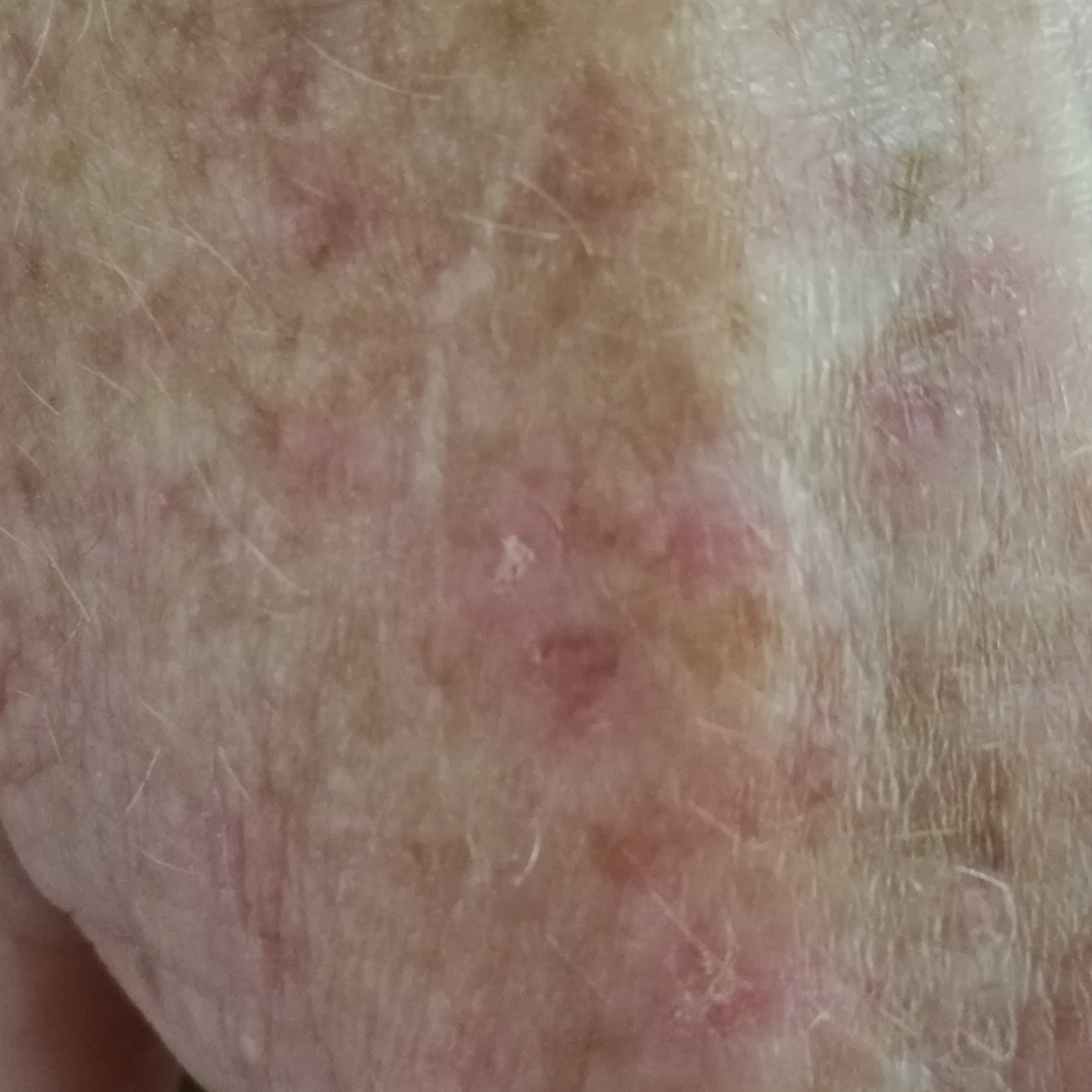{
  "image": "smartphone clinical photo",
  "lesion_location": "a forearm",
  "symptoms": {
    "present": [
      "itching"
    ],
    "absent": [
      "bleeding"
    ]
  },
  "diagnosis": {
    "name": "actinic keratosis",
    "code": "ACK",
    "malignancy": "indeterminate",
    "confirmation": "clinical consensus"
  }
}